A female patient approximately 15 years of age; a dermatoscopic image of a skin lesion: 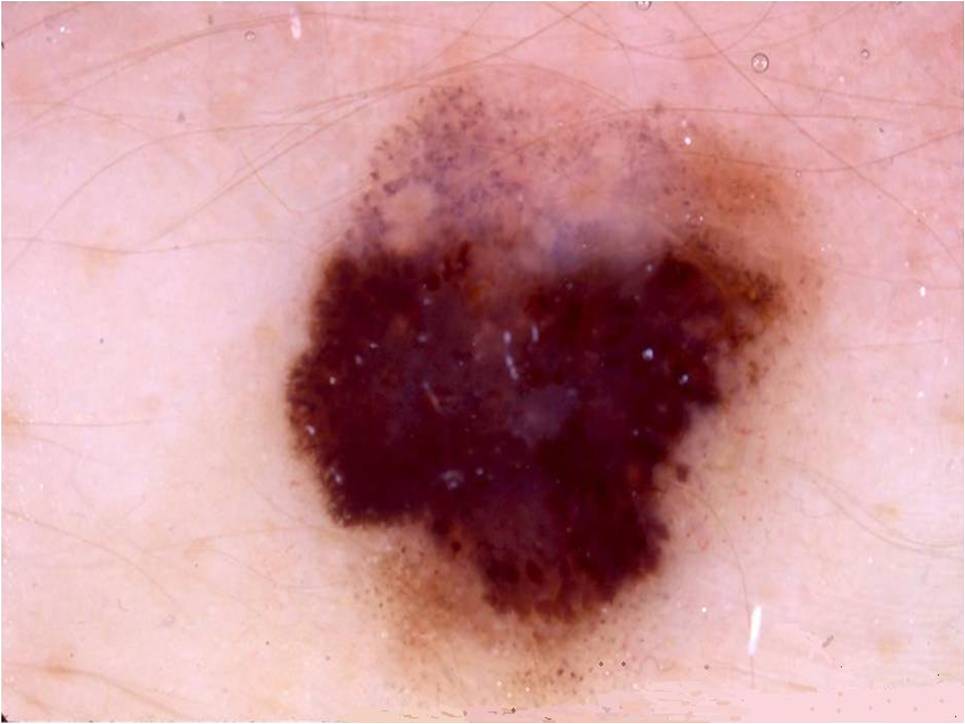Summary:
With coordinates (x1, y1, x2, y2), the visible lesion spans 282, 70, 835, 716. On dermoscopy, the lesion shows pigment network and globules. The lesion takes up a large portion of the image.
Conclusion:
Biopsy-confirmed as a melanoma.